A skin lesion imaged with a dermatoscope, a female patient aged 43 to 47.
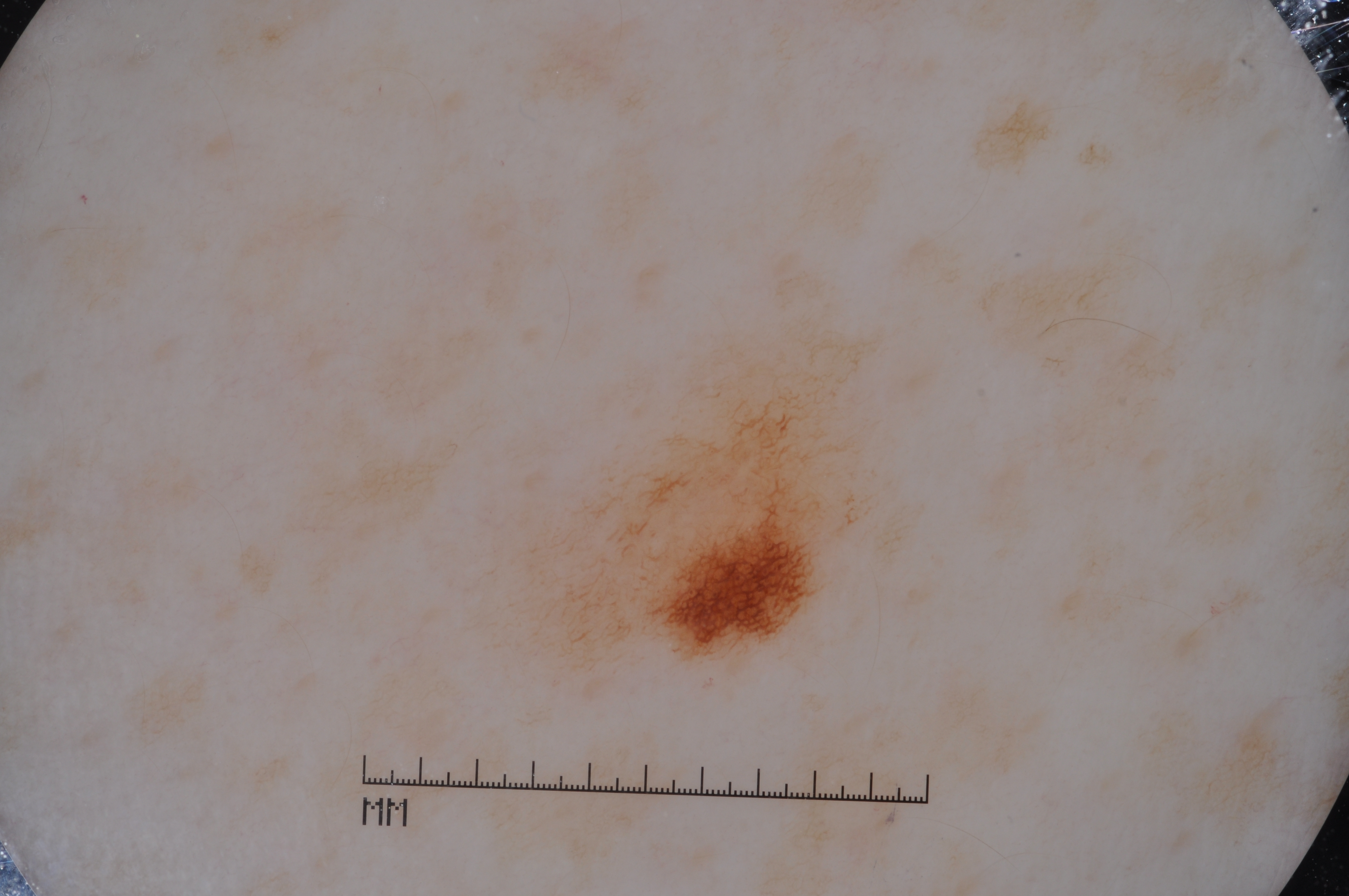Findings:
* features · pigment network
* bounding box · 548/365/864/658
* lesion size · small
* diagnostic label · a melanocytic nevus, a benign lesion